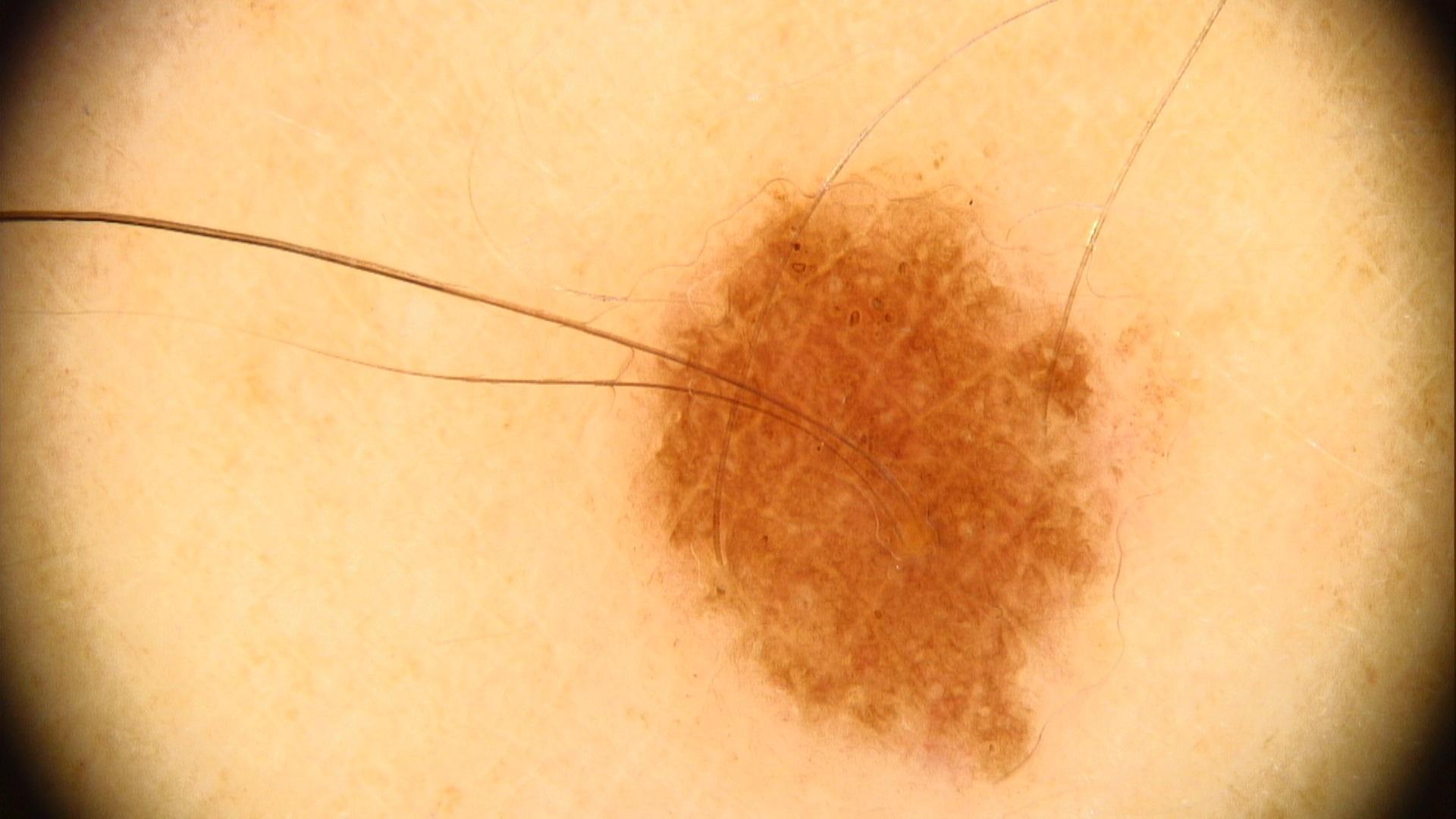Findings:
Recorded as FST III. A male patient aged approximately 40. A skin lesion imaged with a dermatoscope. The chart documents a first-degree relative with melanoma but no prior melanoma. The lesion involves the posterior trunk.
Impression:
Expert review favored a benign, melanocytic lesion — a nevus.